A male subject roughly 70 years of age · the patient is Fitzpatrick phototype II · a contact-polarized dermoscopy image of a skin lesion — 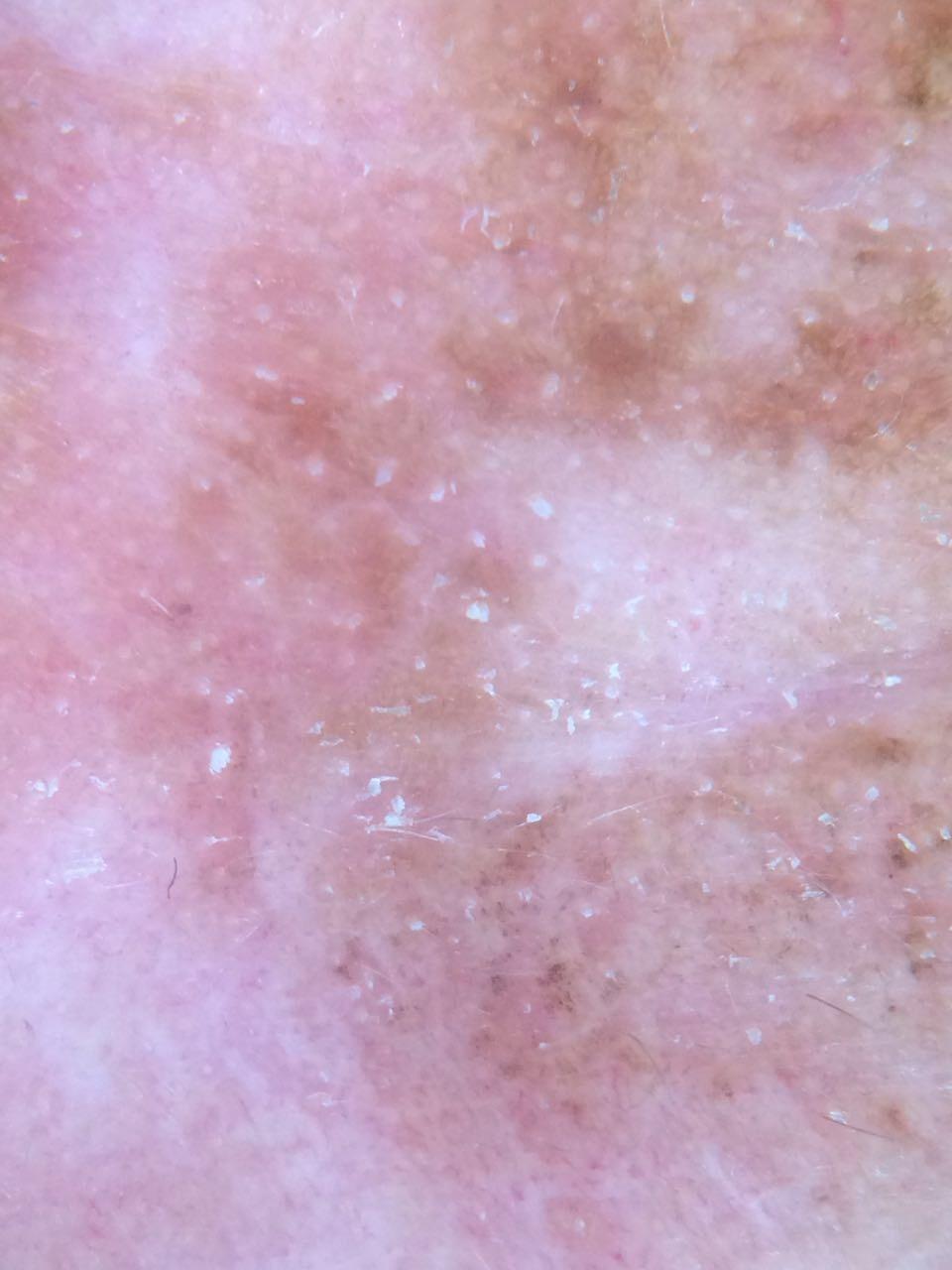diagnosis=Melanoma (biopsy-proven)